A female patient in their mid- to late 40s. A skin lesion imaged with a dermatoscope. Fitzpatrick skin type I.
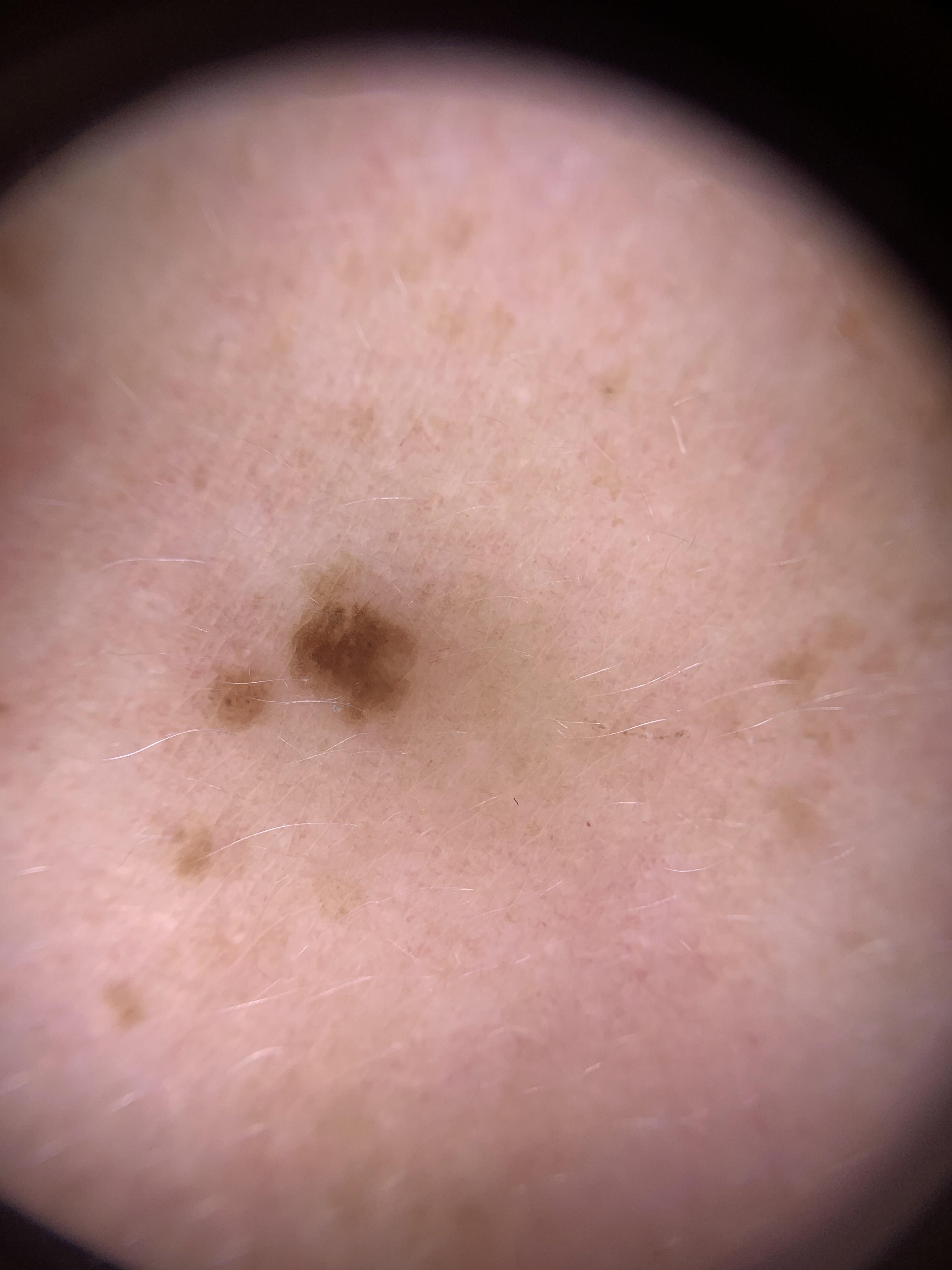Findings: Located on a lower extremity. Conclusion: The clinical impression was a benign lesion — a nevus.